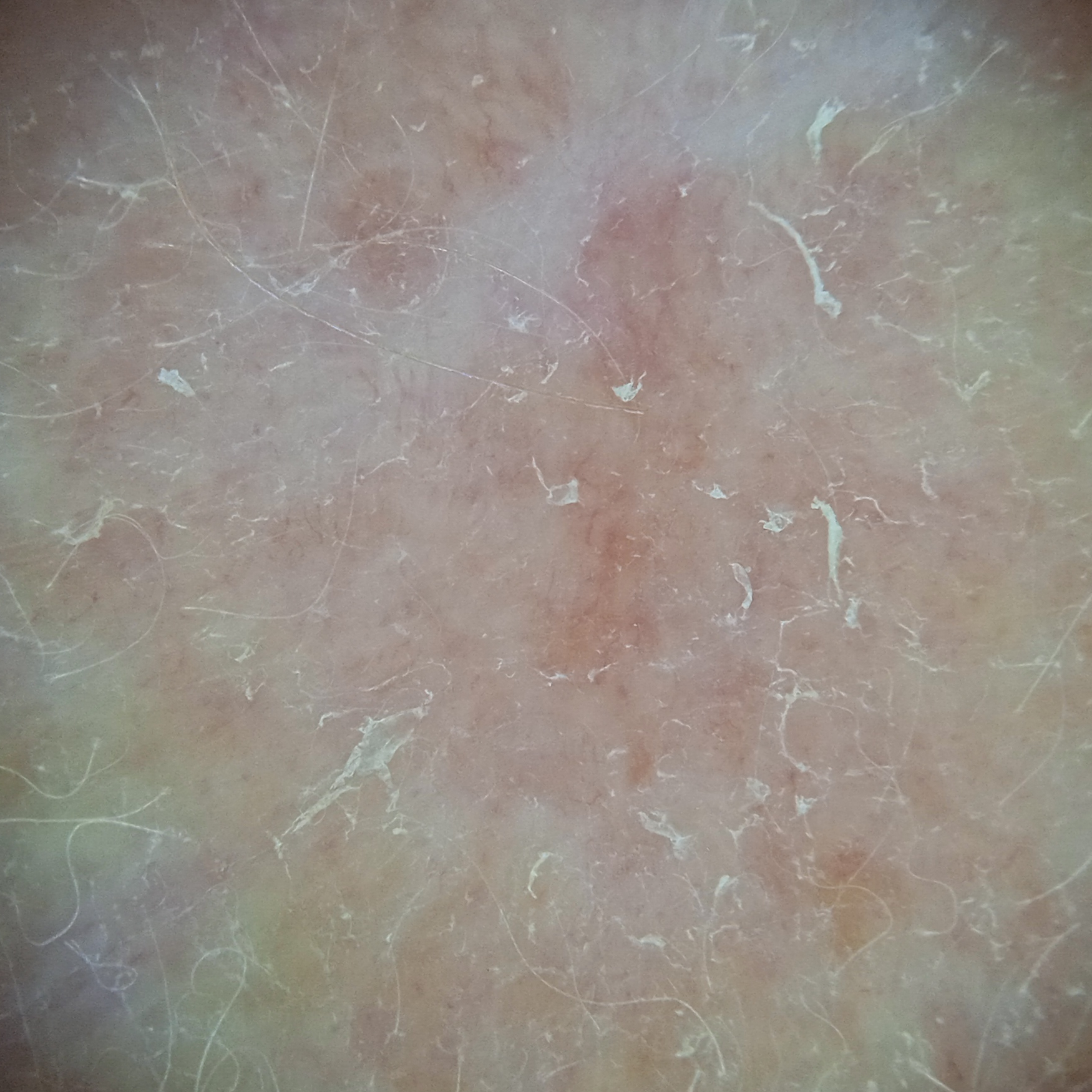| feature | finding |
|---|---|
| risk factors | a personal history of cancer, a family history of skin cancer |
| patient | female, 92 years of age |
| sun reaction | skin tans without first burning |
| clinical context | clinical suspicion of basal cell carcinoma |
| site | the face |
| diameter | 11.5 mm |
| pathology | basal cell carcinoma (biopsy-proven) |